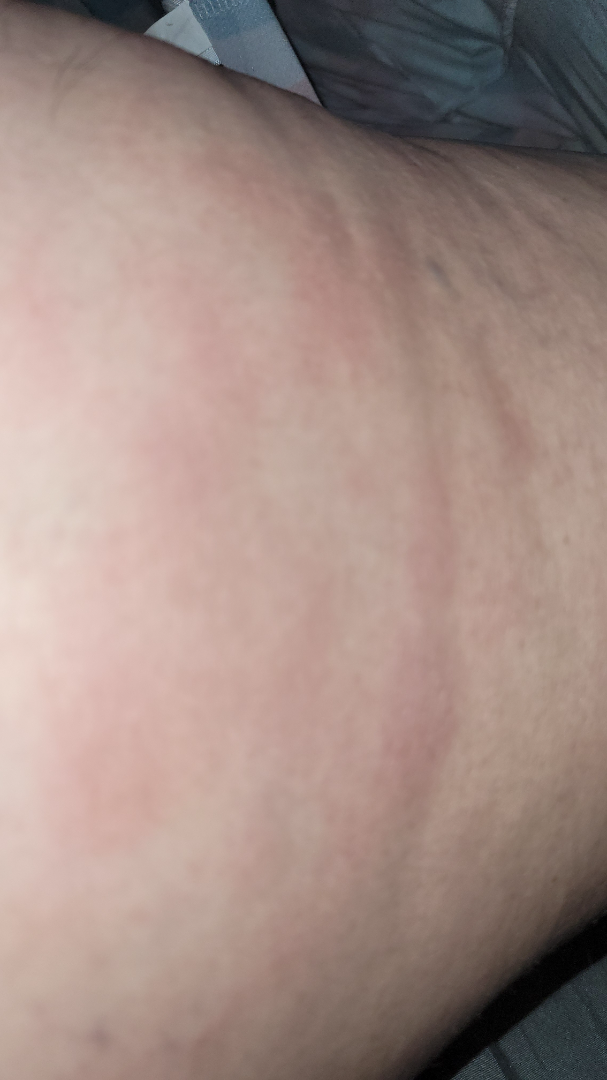assessment=could not be assessed; reported symptoms=none reported; other reported symptoms=joint pain; symptom duration=one to four weeks; self-categorized as=a rash; site=leg; patient=female, age 40–49; lesion texture=flat; photo taken=close-up.